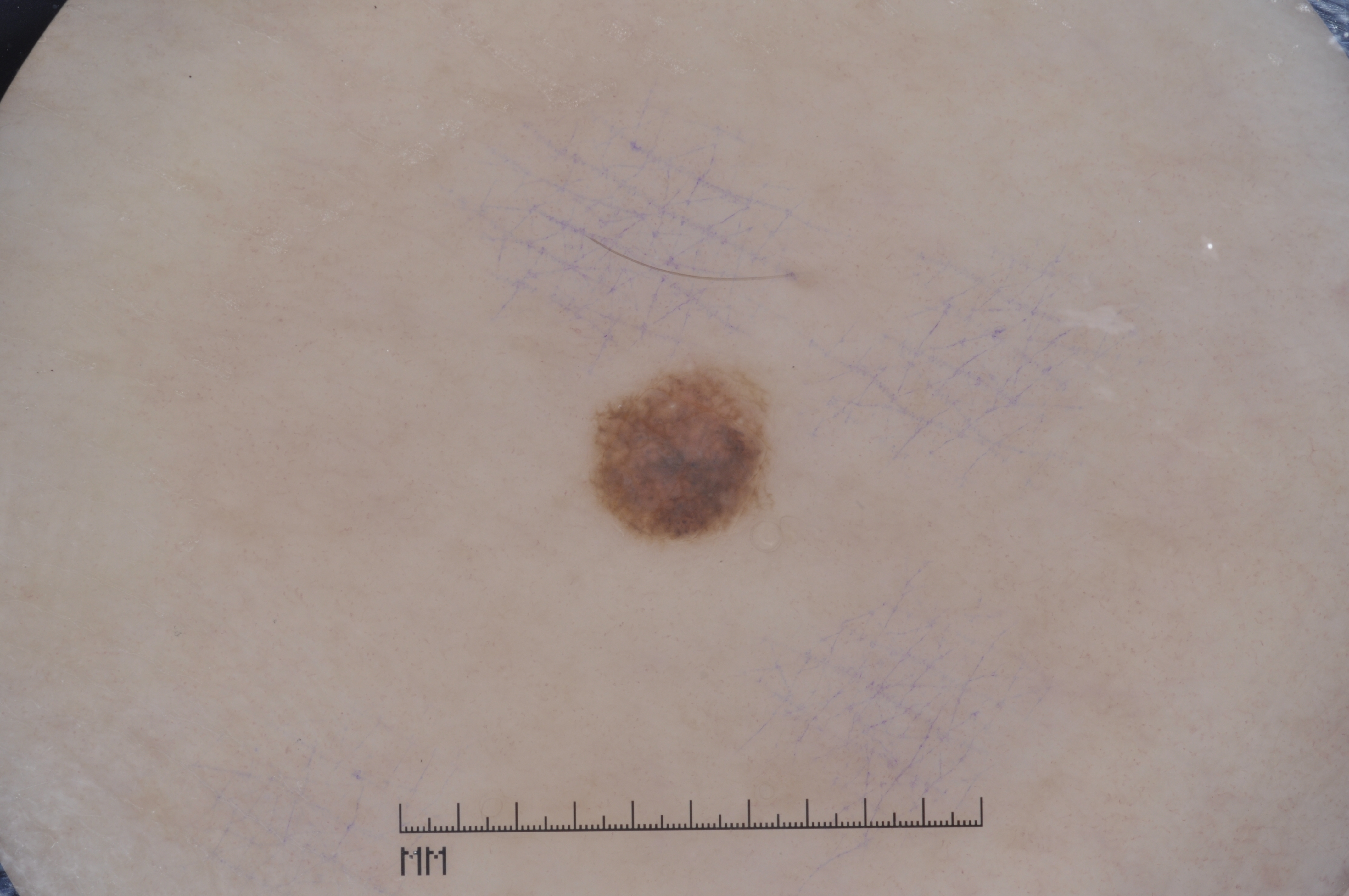A skin lesion imaged with a dermatoscope.
A female subject, approximately 55 years of age.
Dermoscopic review identifies pigment network and milia-like cysts; no streaks or negative network.
With coordinates (x1, y1, x2, y2), the lesion's extent is [590, 365, 769, 539].
Clinically diagnosed as a melanocytic nevus, a benign lesion.